A skin lesion imaged with a dermatoscope: 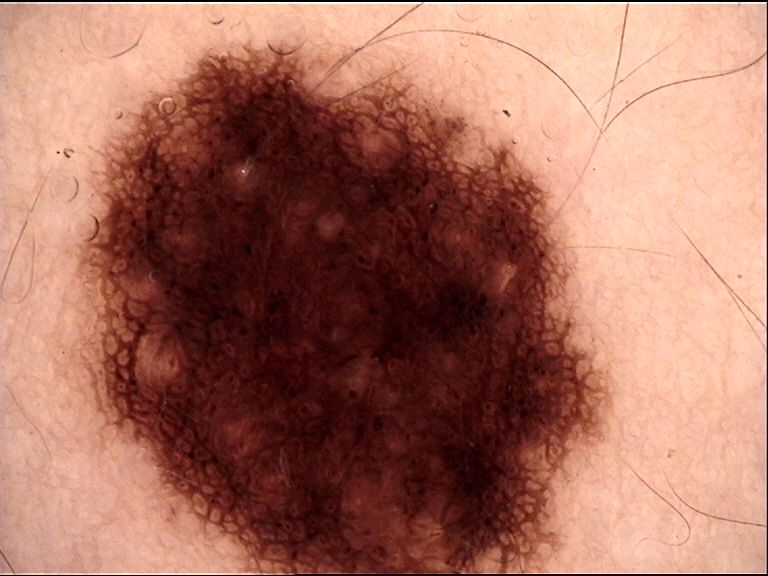Classified as a dysplastic junctional nevus.